The photo was captured at an angle: 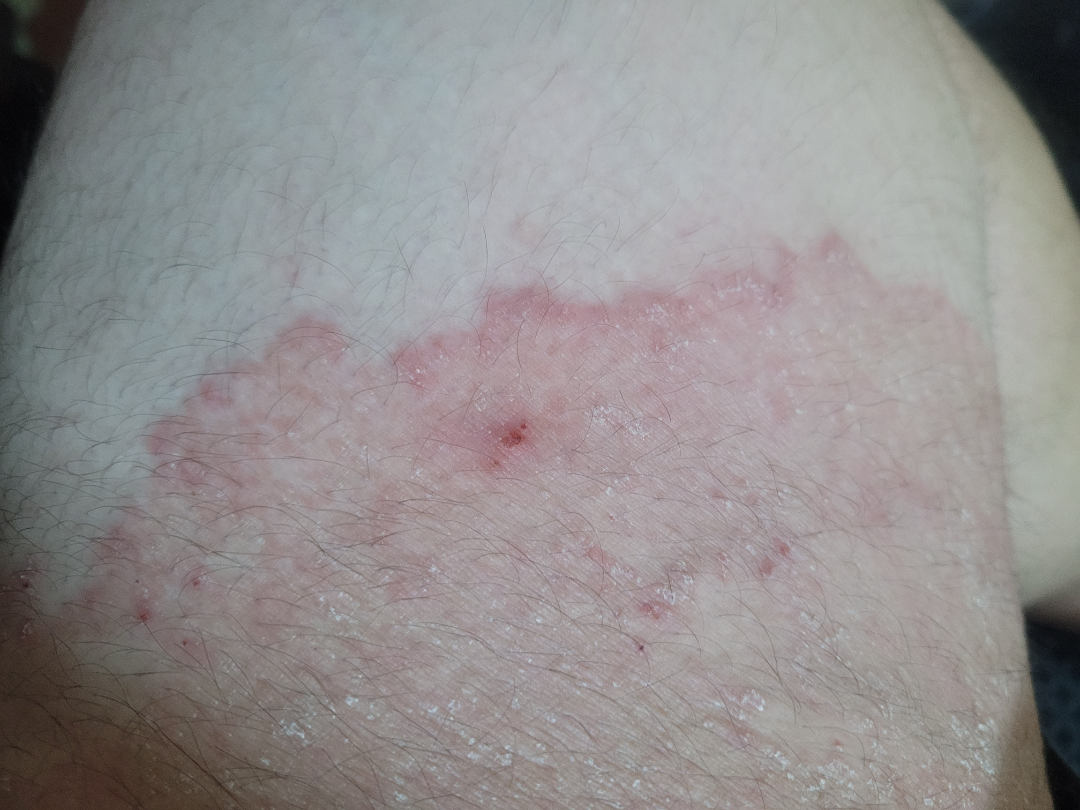Impression:
In keeping with Tinea.